An image taken at an angle · the affected area is the top or side of the foot, head or neck, sole of the foot, back of the torso and palm — 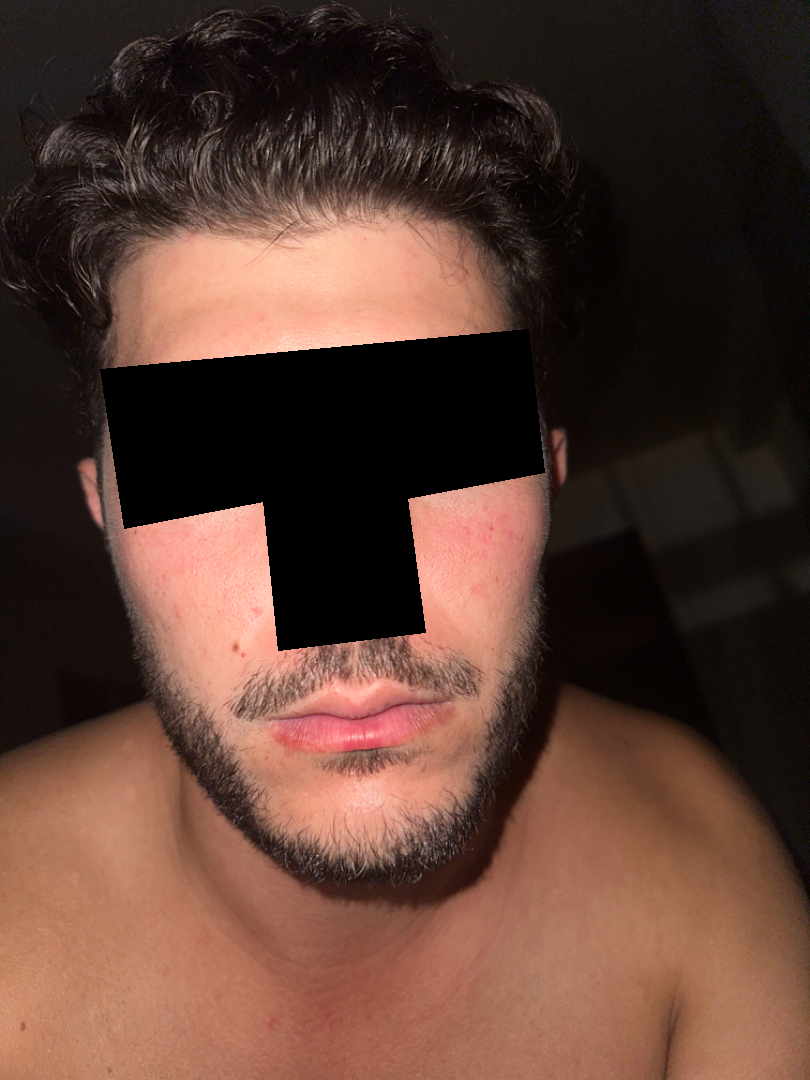Skin tone: FST III; human graders estimated Monk skin tone scale 3 (US pool) or 2 (India pool).
The patient described the issue as a rash.
The lesion is associated with bothersome appearance.
The patient notes the lesion is flat.
The patient notes the condition has been present for less than one week.
On teledermatology review, the leading consideration is Acne.